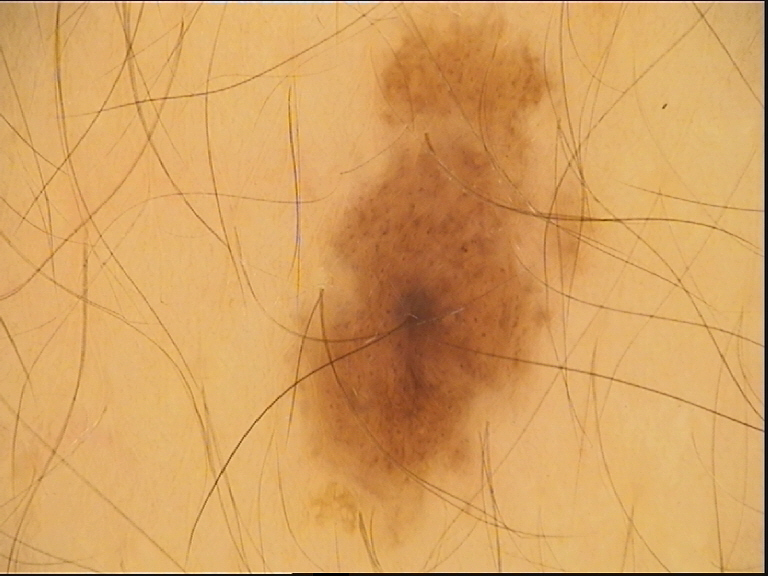class — dysplastic junctional nevus (expert consensus).